A skin lesion imaged with a dermatoscope.
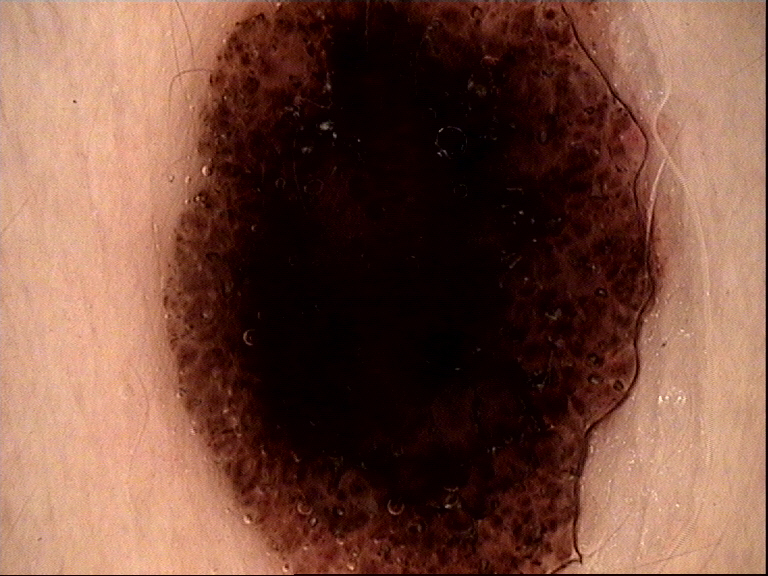Conclusion:
Diagnosed as a dysplastic compound nevus.